A dermatoscopic image of a skin lesion:
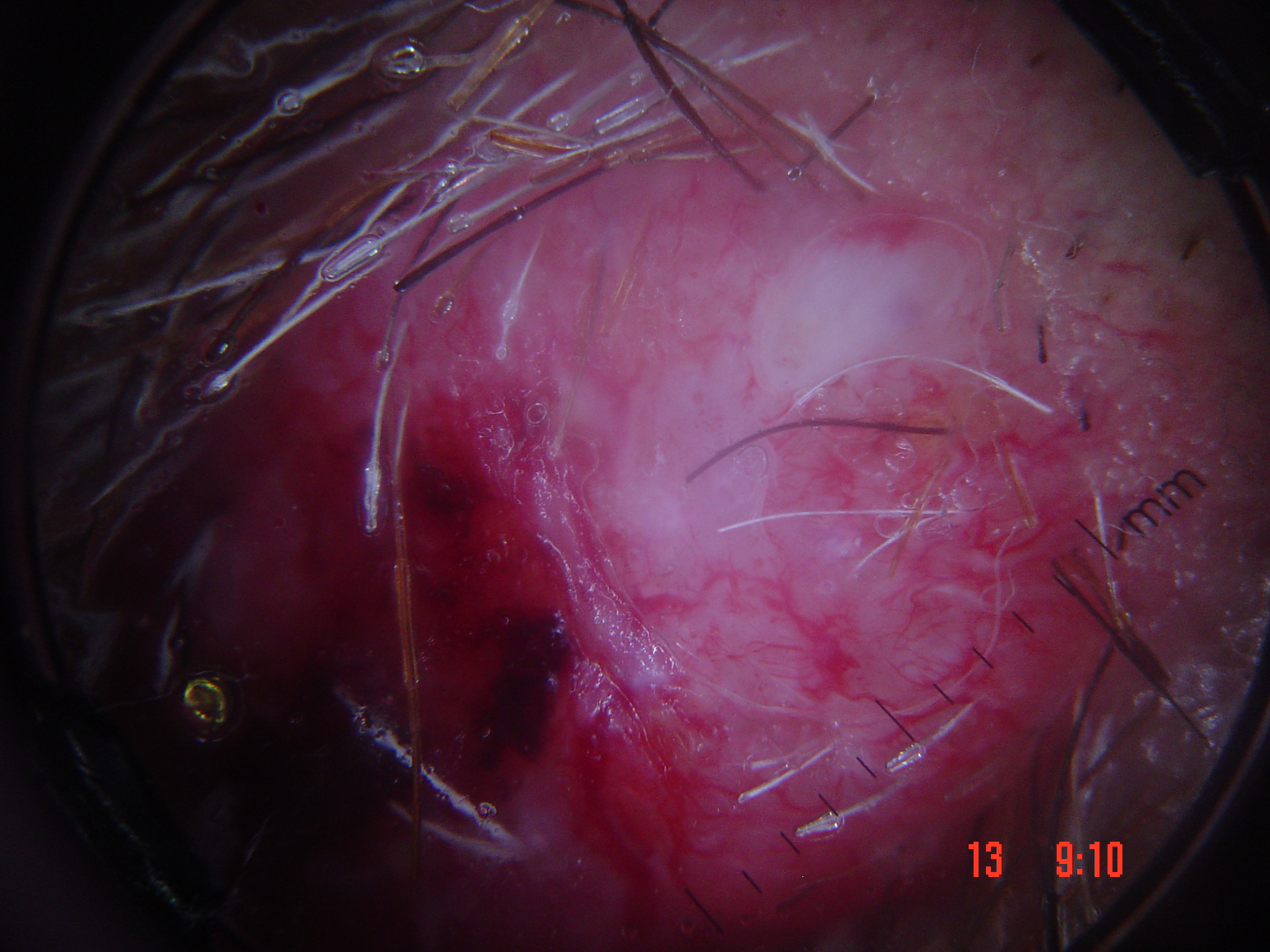The architecture is that of a keratinocytic lesion. Biopsy-confirmed as a skin cancer — a squamous cell carcinoma.